Recorded as FST II · a male patient in their early 50s · a smartphone photograph of a skin lesion — 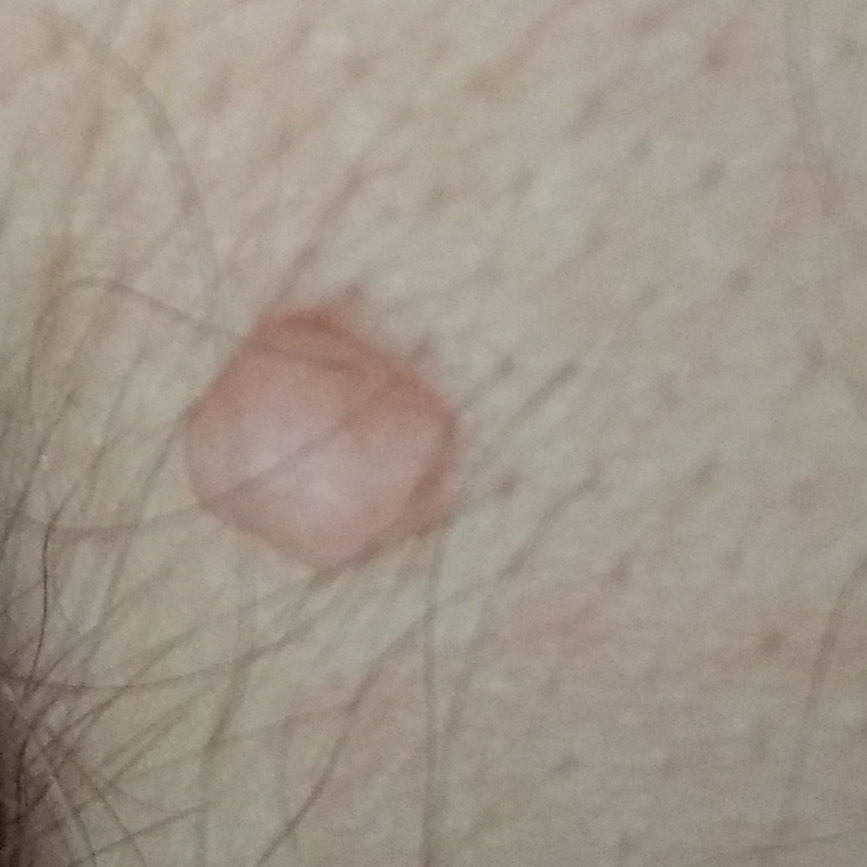The lesion involves a thigh.
Measuring about 10 × 8 mm.
The patient reports that the lesion is elevated.
Expert review favored a nevus.